The patient described the issue as a rash; reported duration is one to four weeks; located on the back of the hand; the photograph was taken at an angle; female patient, age 18–29 — 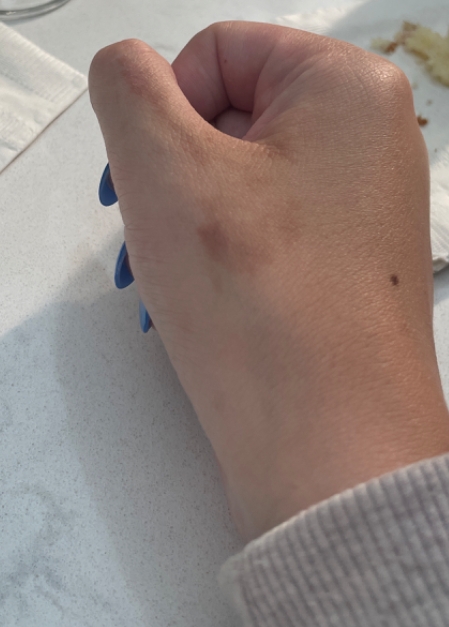{"differential": "Photodermatitis"}